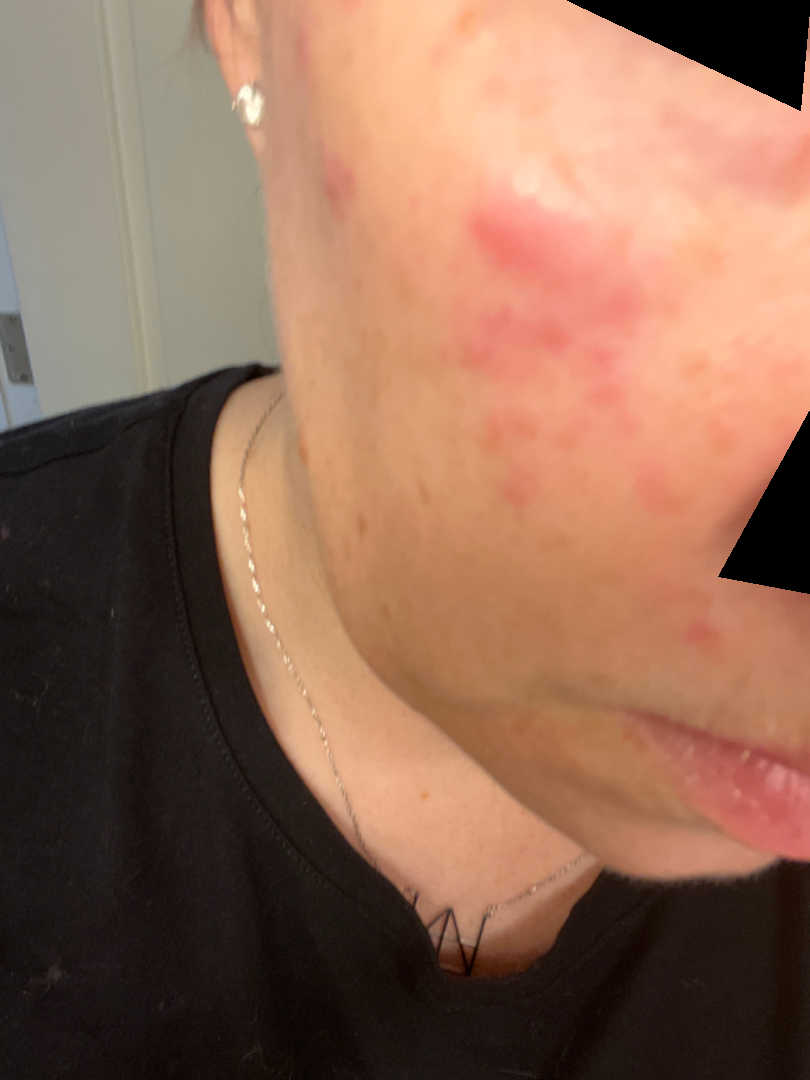The lesion is described as raised or bumpy.
Symptoms reported: enlargement.
The lesion involves the head or neck.
The patient is 40–49, female.
No associated systemic symptoms reported.
Fitzpatrick III; human graders estimated Monk skin tone scale 2.
An image taken at an angle.
On photographic review: most consistent with Acne; an alternative is Rosacea.